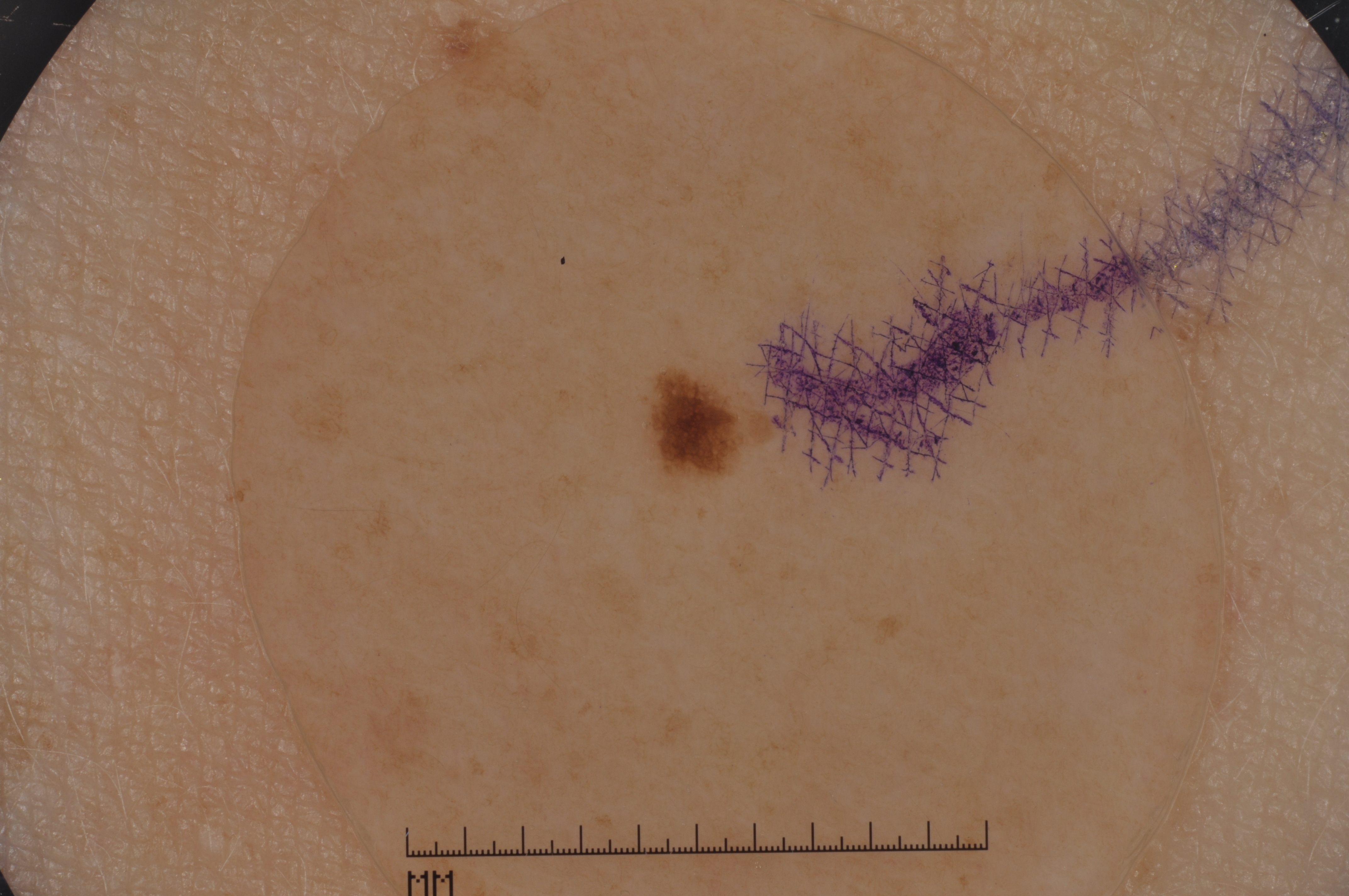Q: What kind of image is this?
A: dermoscopy of a skin lesion
Q: Where is the lesion located?
A: [636,366,780,491]
Q: What does dermoscopy show?
A: pigment network
Q: How large is the lesion within the image?
A: small
Q: What did the assessment conclude?
A: a melanocytic nevus